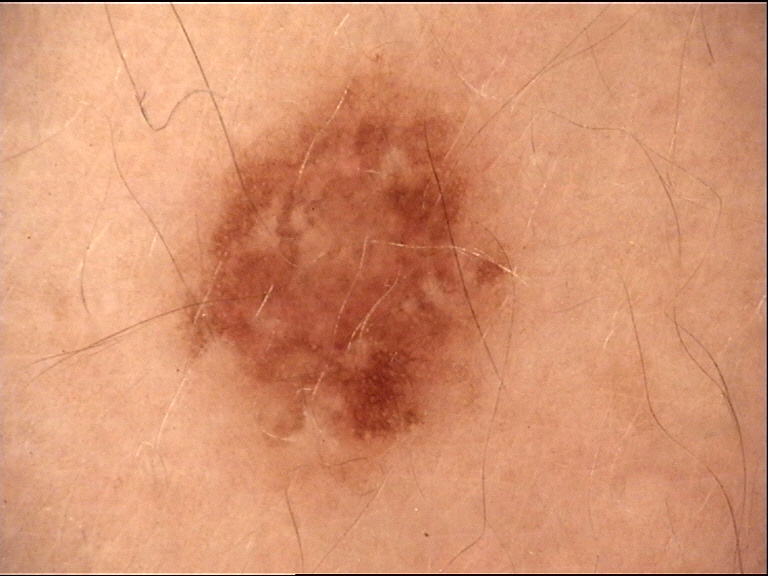Q: What is the imaging modality?
A: dermatoscopy
Q: What was the diagnostic impression?
A: dysplastic junctional nevus (expert consensus)